The contributor notes the condition has been present for less than one week; the patient described the issue as a rash; the photograph was taken at an angle; the affected area is the leg; no constitutional symptoms were reported: 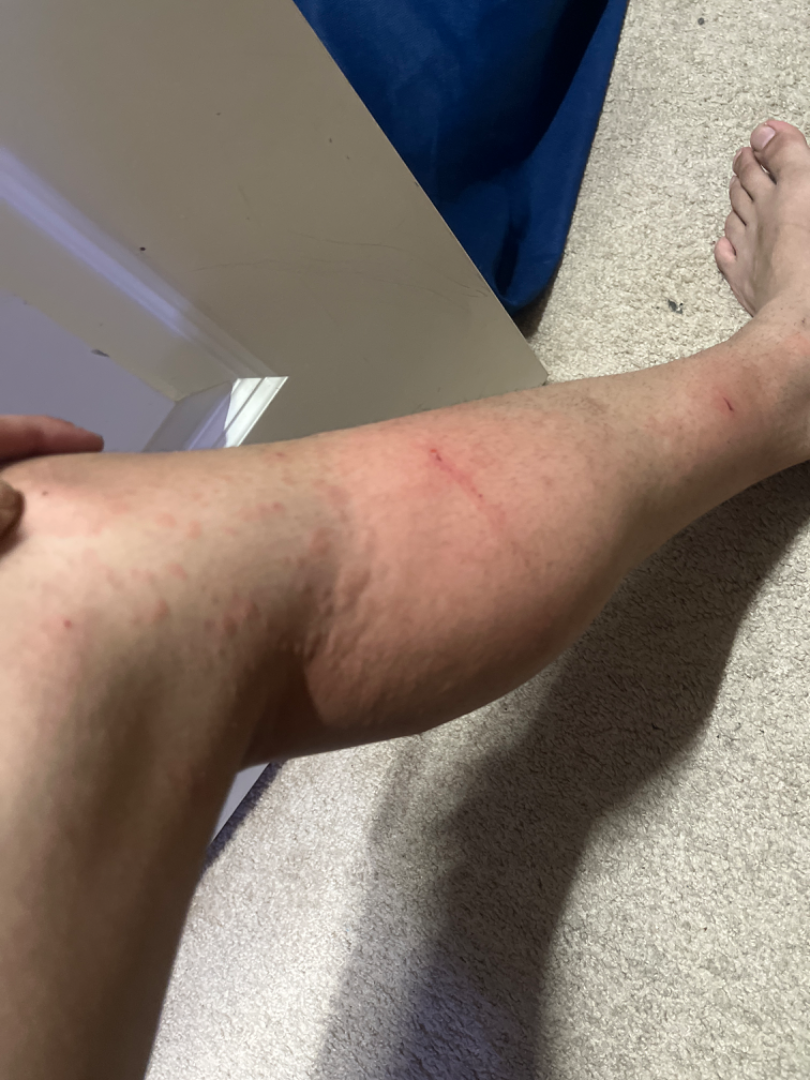On remote dermatologist review: Urticaria (primary); Allergic Contact Dermatitis (considered).